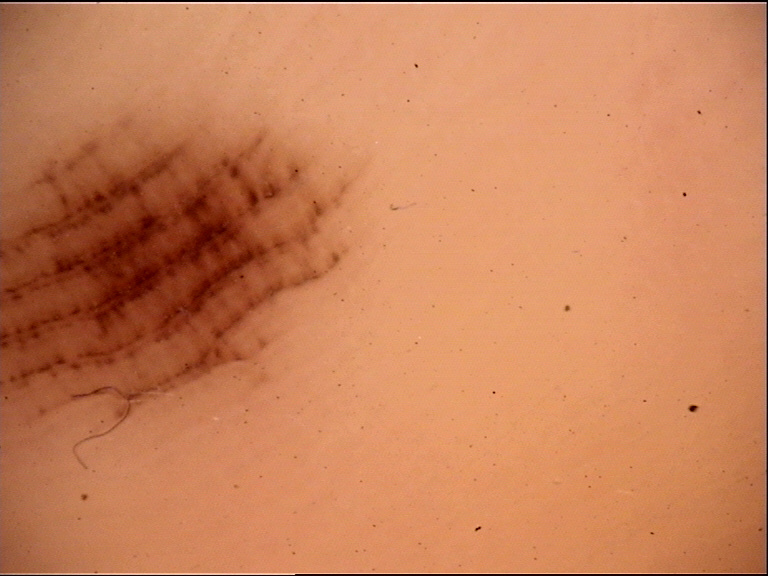{"image": "dermatoscopy", "lesion_type": {"main_class": "banal", "pattern": "junctional"}, "diagnosis": {"name": "acral junctional nevus", "code": "ajb", "malignancy": "benign", "super_class": "melanocytic", "confirmation": "expert consensus"}}